Dermoscopy of a skin lesion: 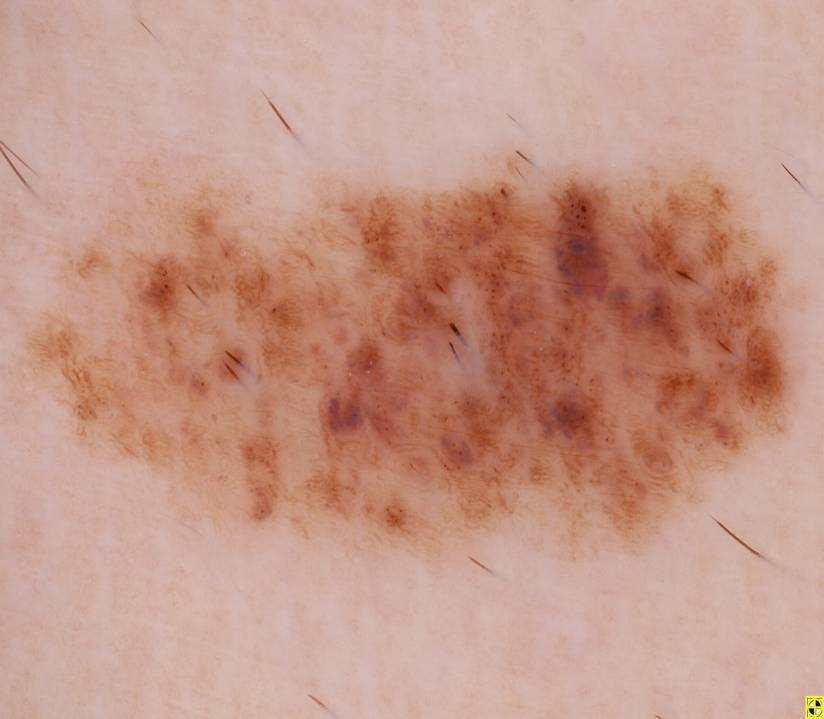In (x1, y1, x2, y2) order, lesion location: 8 148 806 564.
The diagnostic assessment was a melanocytic nevus.